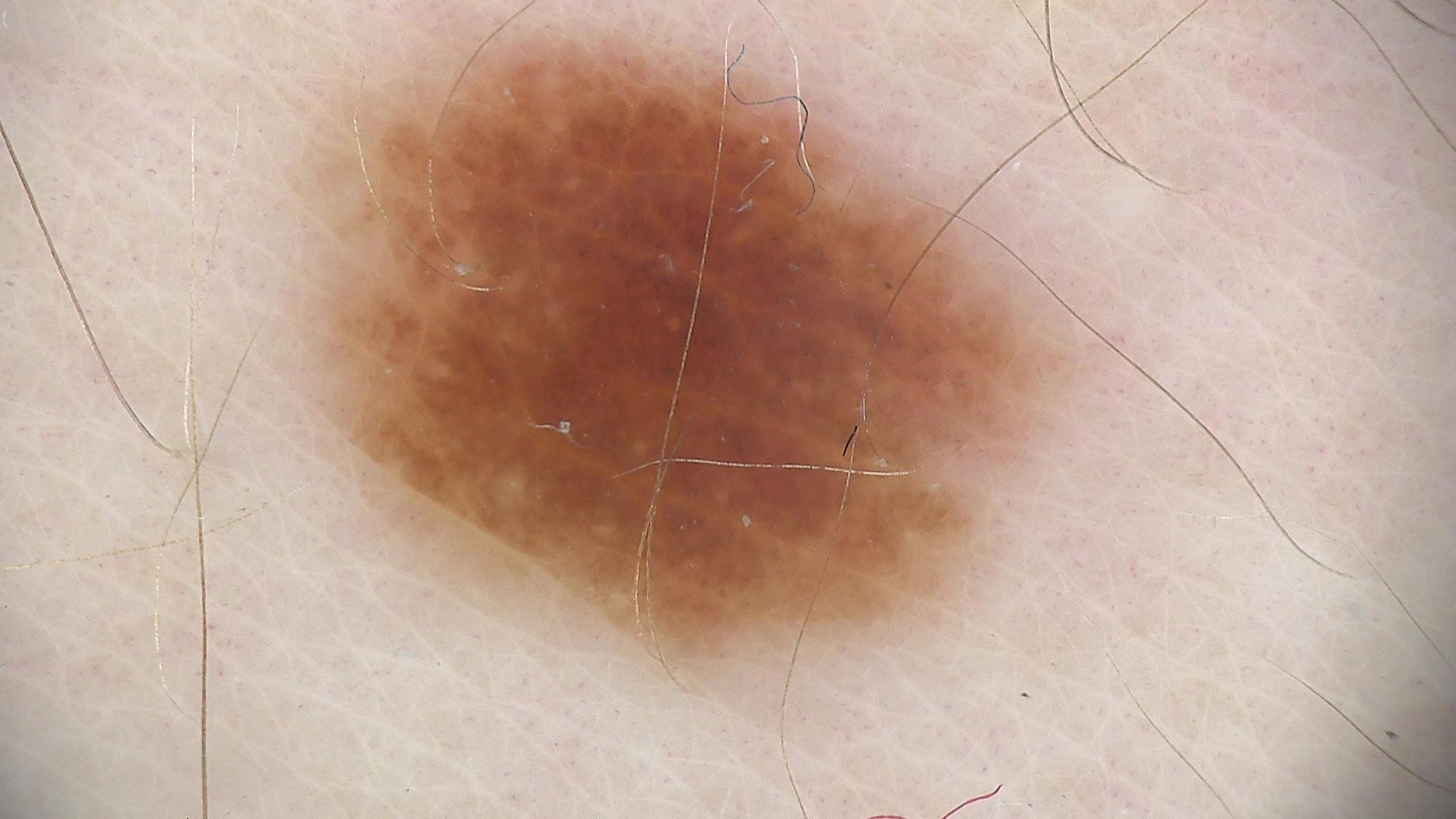Q: What is the imaging modality?
A: dermatoscopy
Q: What was the diagnostic impression?
A: dysplastic junctional nevus (expert consensus)